A dermoscopic photograph of a skin lesion.
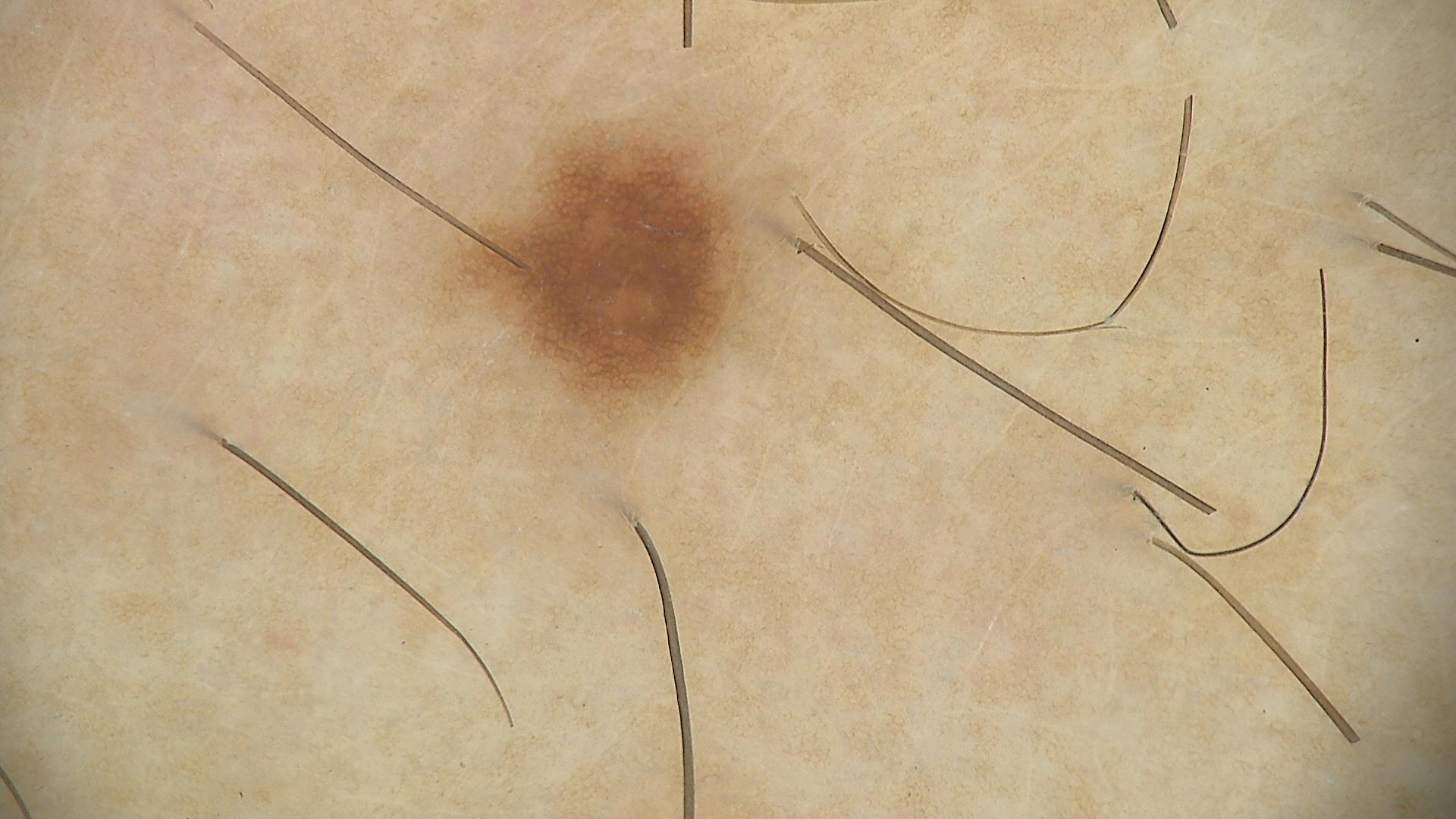<lesion>
<diagnosis>
<name>junctional nevus</name>
<code>jb</code>
<malignancy>benign</malignancy>
<super_class>melanocytic</super_class>
<confirmation>expert consensus</confirmation>
</diagnosis>
</lesion>